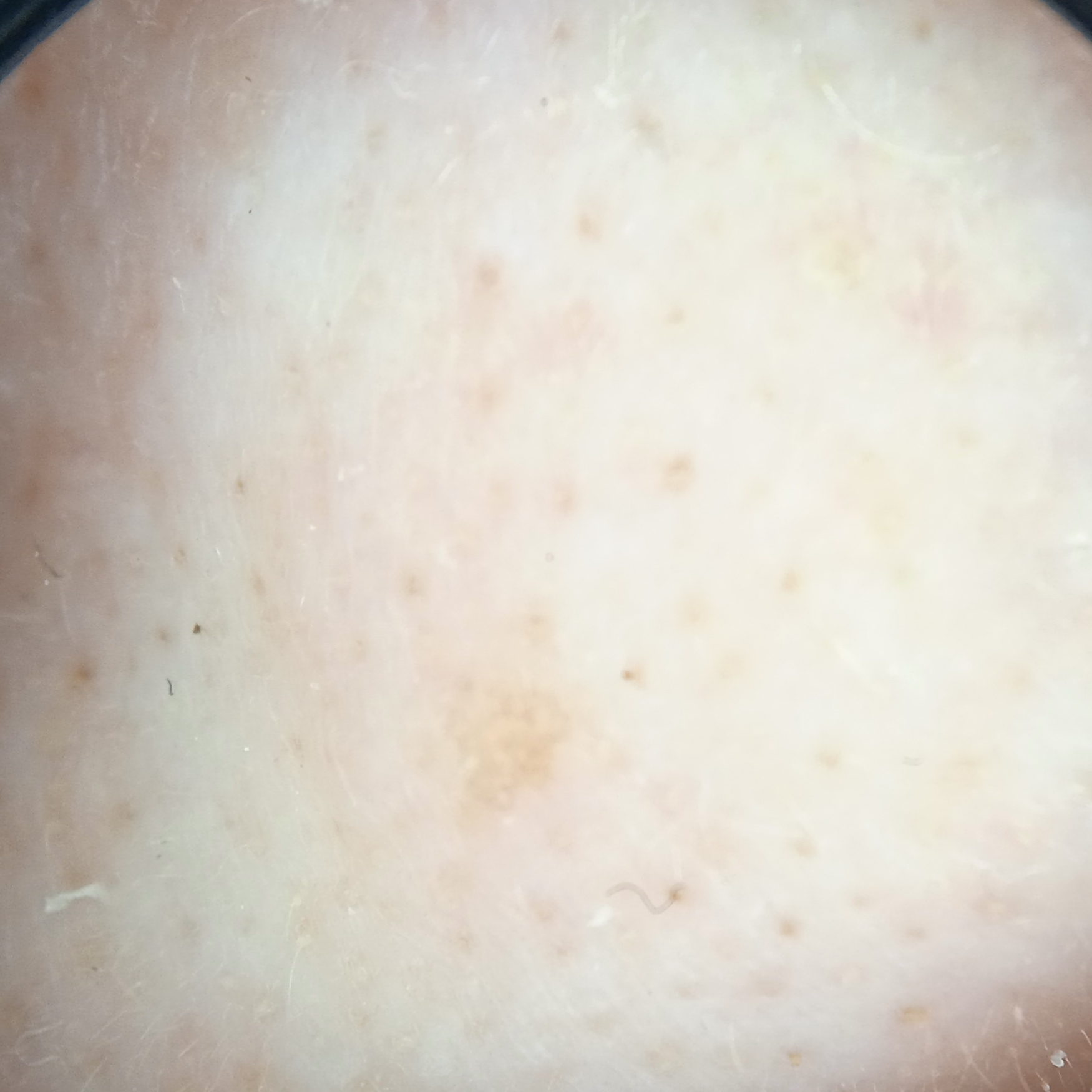The diagnostic impression was an actinic keratosis.